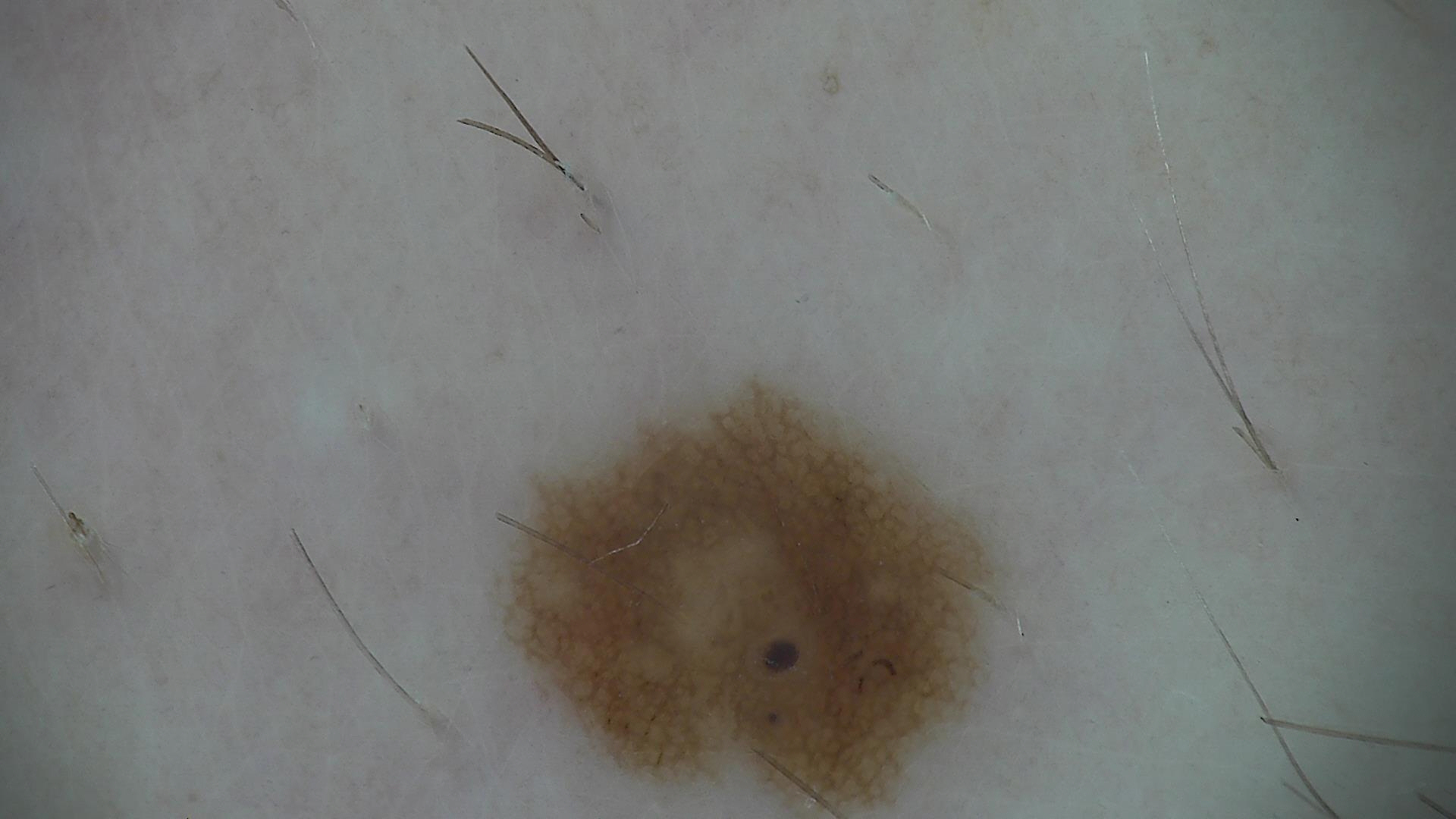A skin lesion imaged with a dermatoscope.
The diagnostic label was a dysplastic junctional nevus.